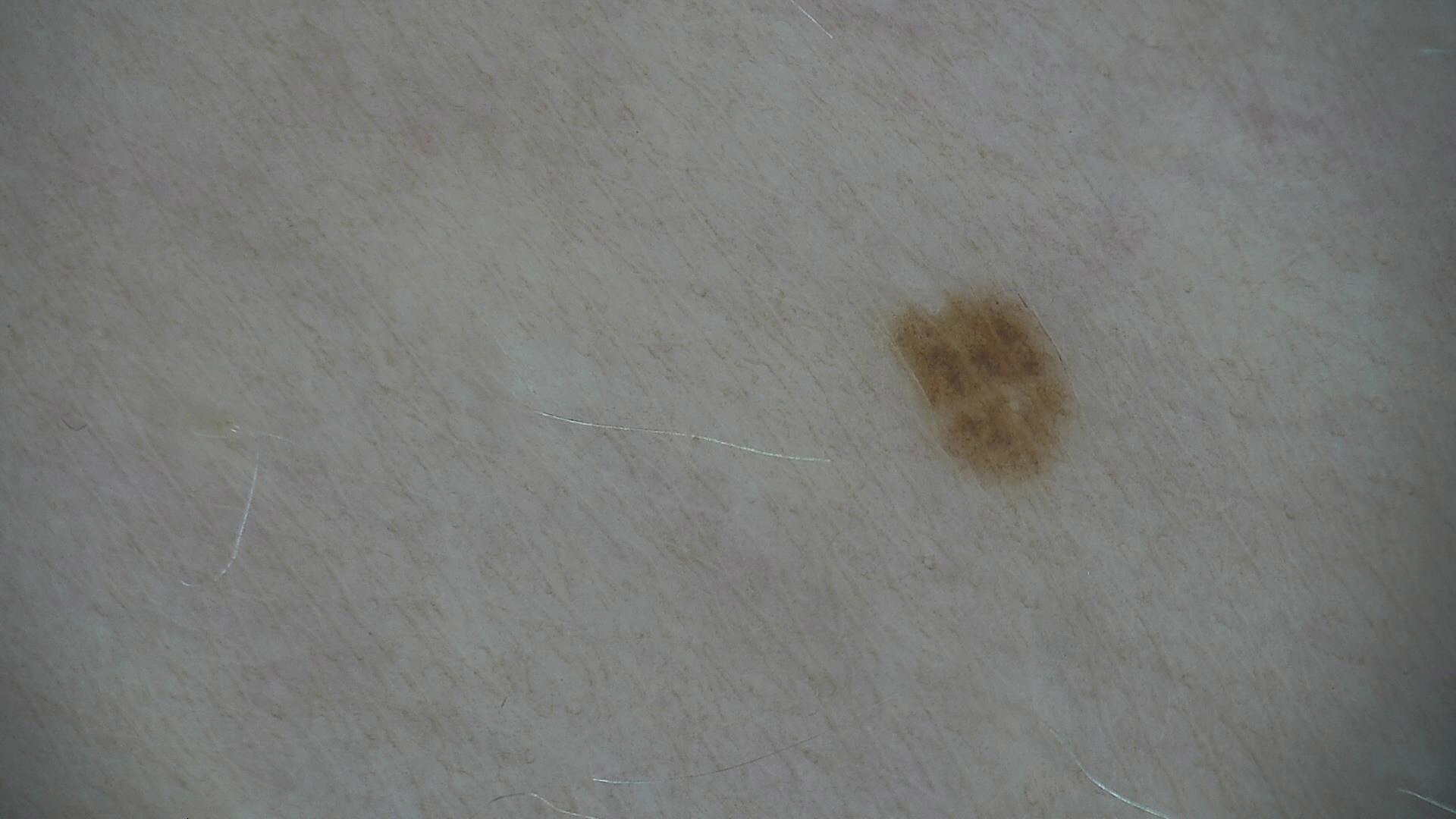A skin lesion imaged with a dermatoscope.
The diagnosis was a benign lesion — a dysplastic junctional nevus.